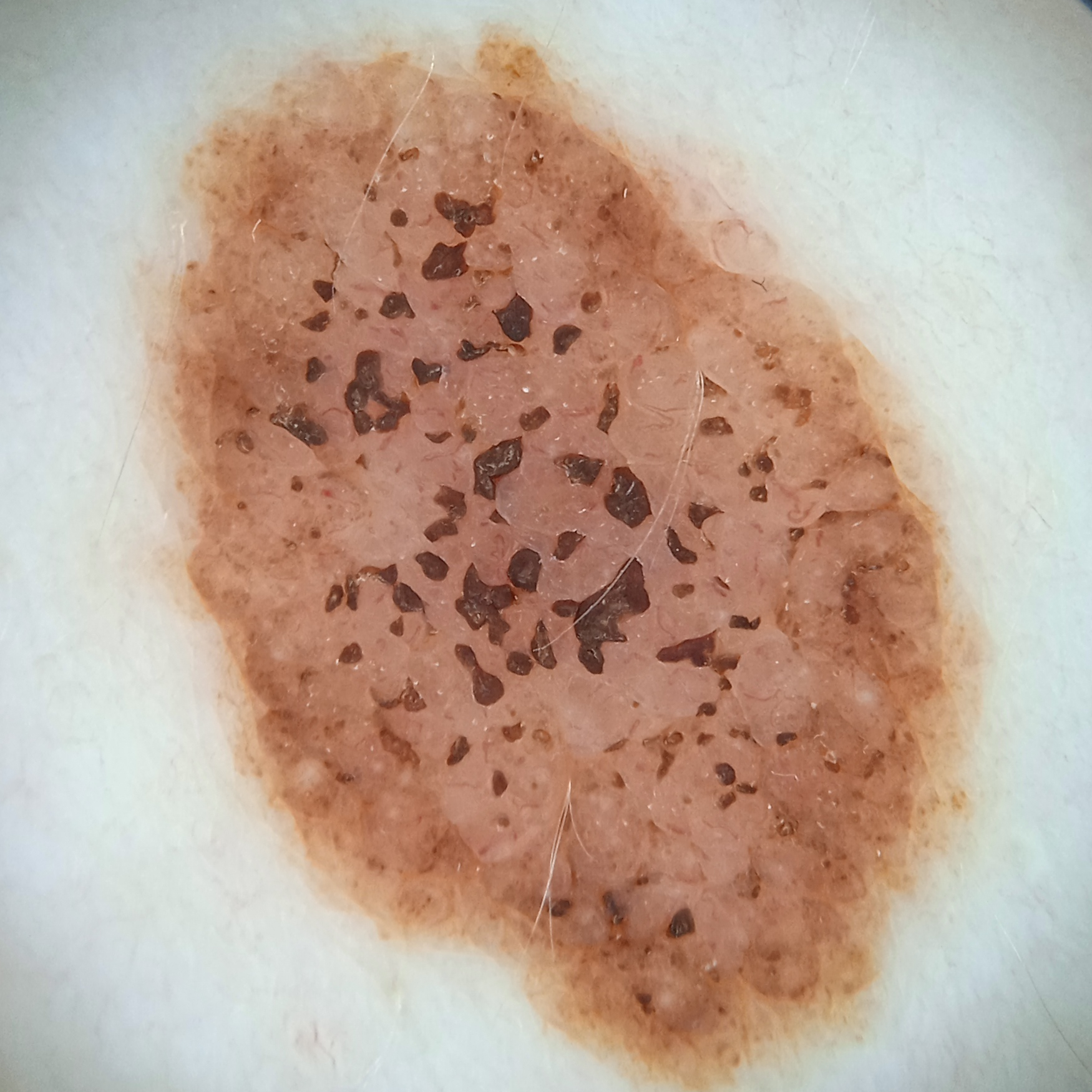A female subject 26 years old.
A dermatoscopic image of a skin lesion.
Collected as part of a research study, without a referral diagnosis.
The lesion was assessed as a melanocytic nevus.